The referring clinician suspected basal cell carcinoma; a dermatoscopic image of a skin lesion; the patient describes having few moles overall:
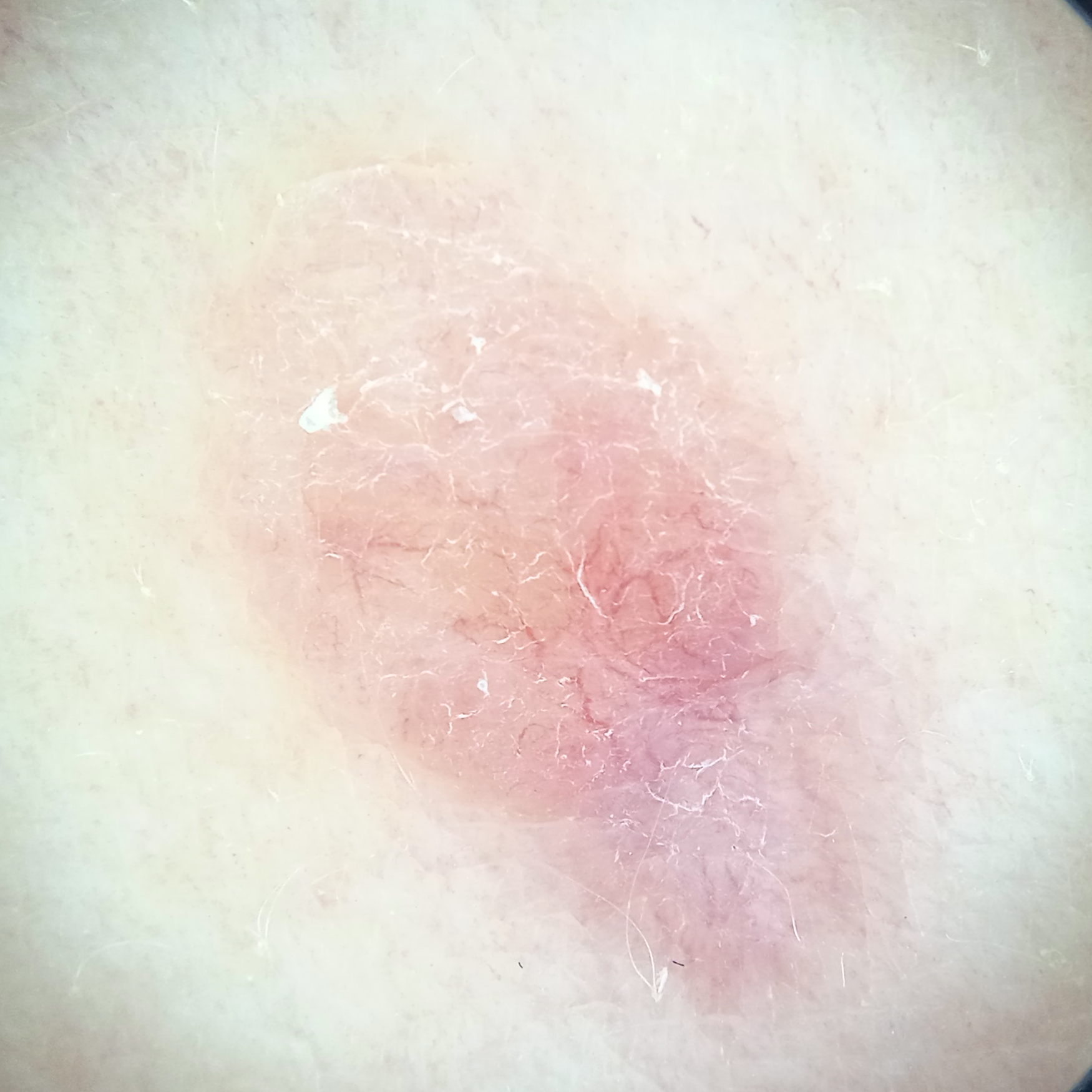The lesion is located on the back. Measuring roughly 12.3 mm. Confirmed on histopathology as a basal cell carcinoma, following excision, with a measured tumor thickness of 1.1 mm.